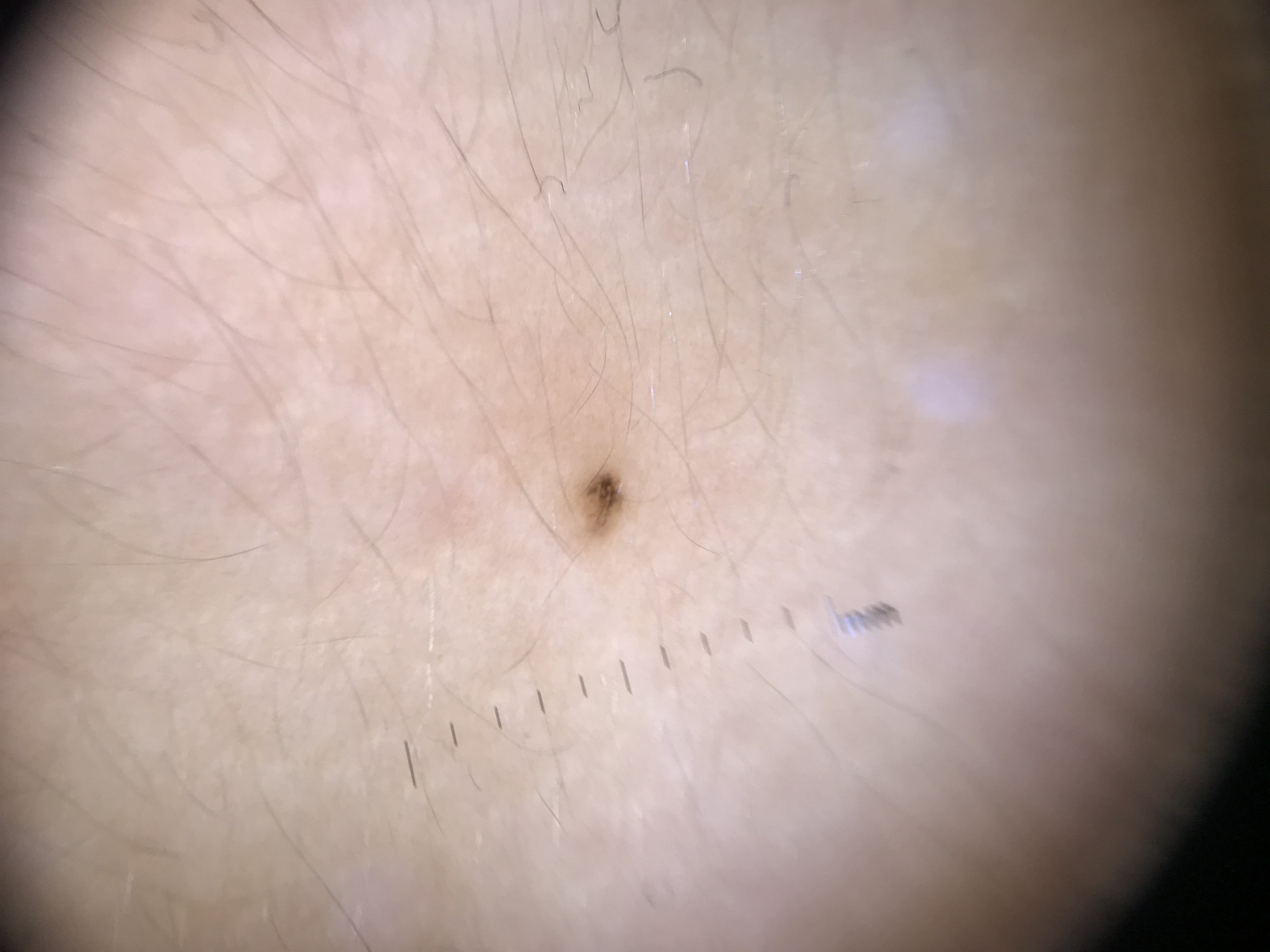Conclusion: Labeled as a dysplastic junctional nevus.